The arm, leg, sole of the foot, palm and head or neck are involved; female patient, age 18–29; this image was taken at an angle:
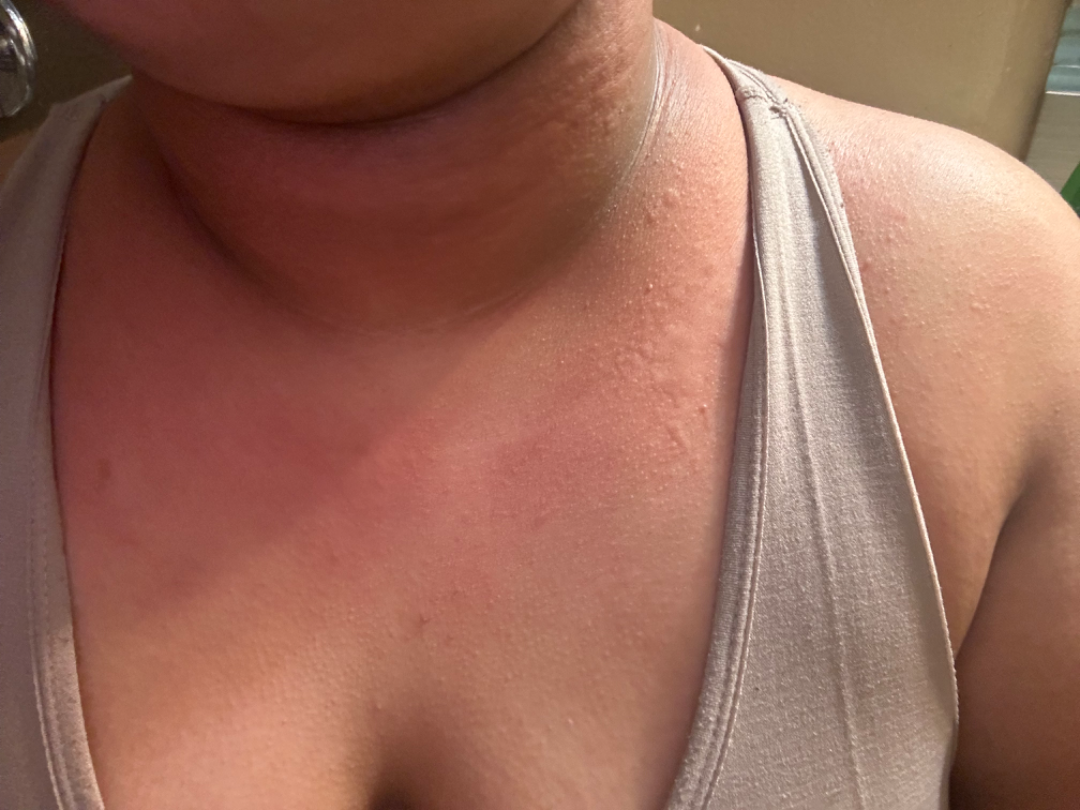| feature | finding |
|---|---|
| impression | one reviewing dermatologist: most likely Urticaria; also on the differential is Drug Rash |